This is a close-up image. The affected area is the back of the torso. The subject is 30–39, female — 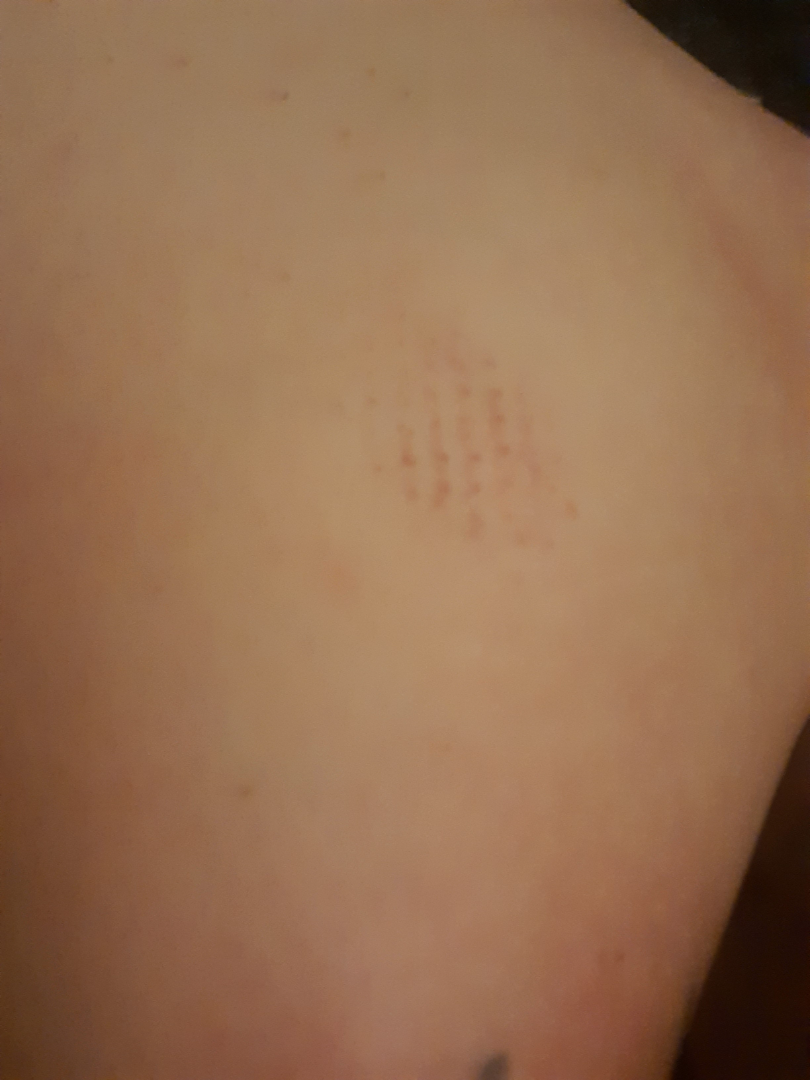<case>
  <assessment>not assessable</assessment>
  <systemic_symptoms>none reported</systemic_symptoms>
  <skin_tone>
    <fitzpatrick>I</fitzpatrick>
    <fitzpatrick_source>self_reported</fitzpatrick_source>
  </skin_tone>
  <symptoms>none reported</symptoms>
  <patient_category>a rash</patient_category>
  <duration>about one day</duration>
</case>